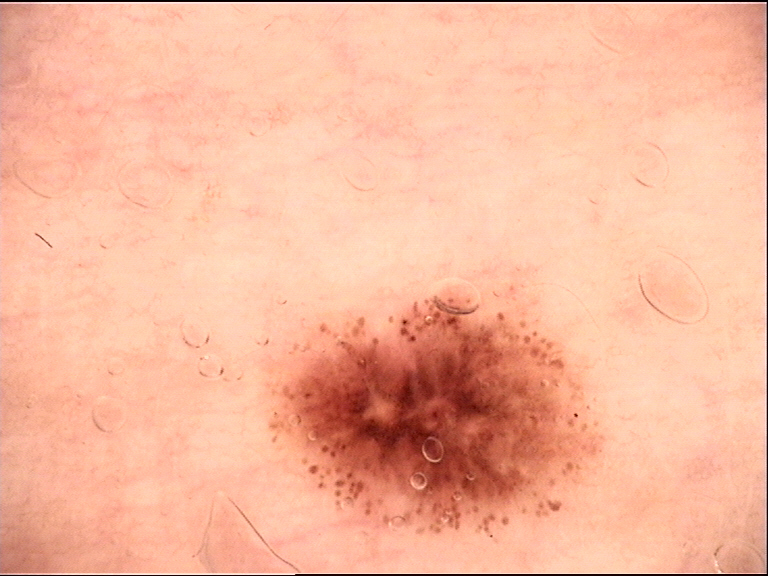– class — dysplastic junctional nevus (expert consensus)